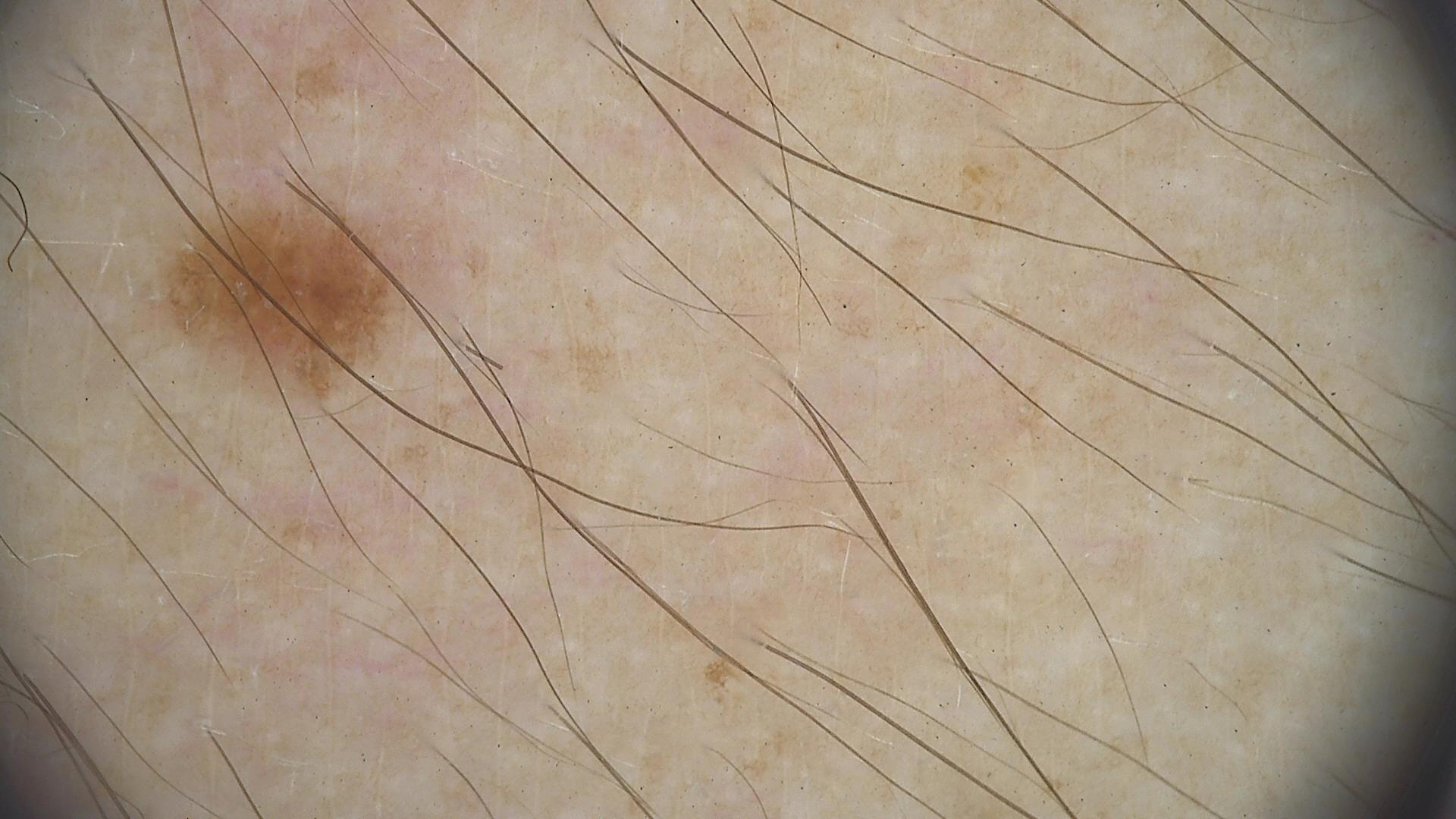A dermoscopy image of a single skin lesion. The diagnostic label was a dysplastic junctional nevus.